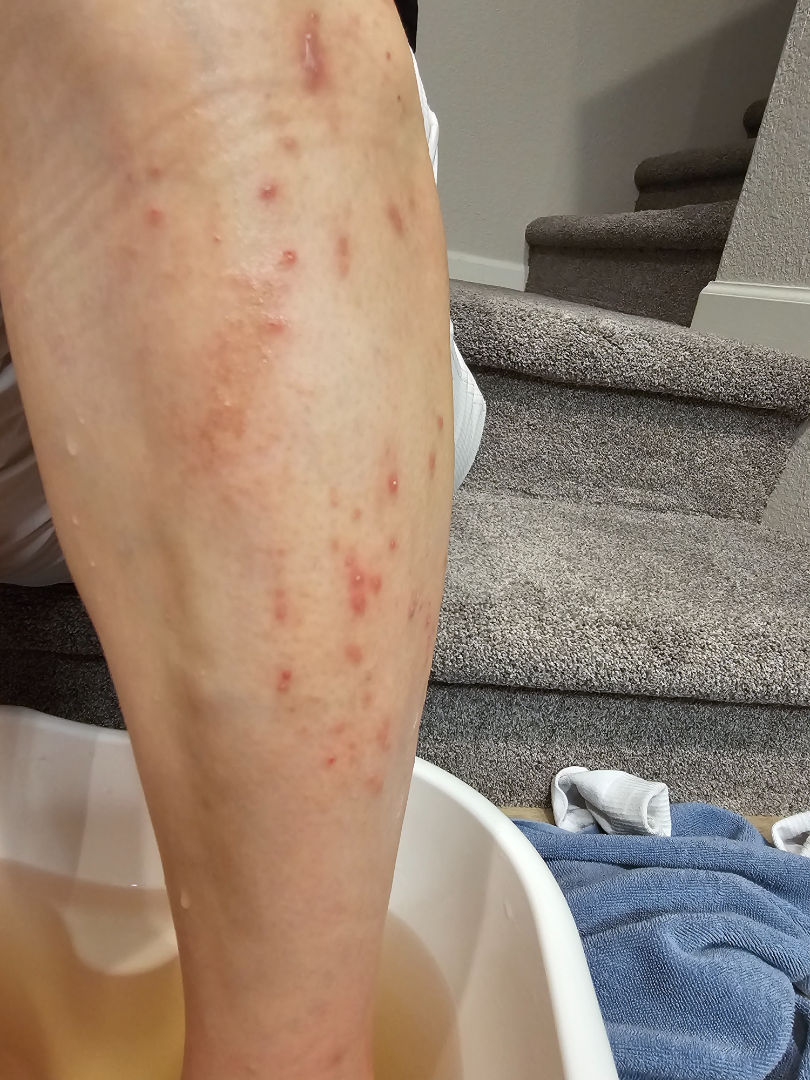An image taken at an angle. The leg is involved. The patient is female. Perforating dermatosis and Psoriasis were considered with similar weight.